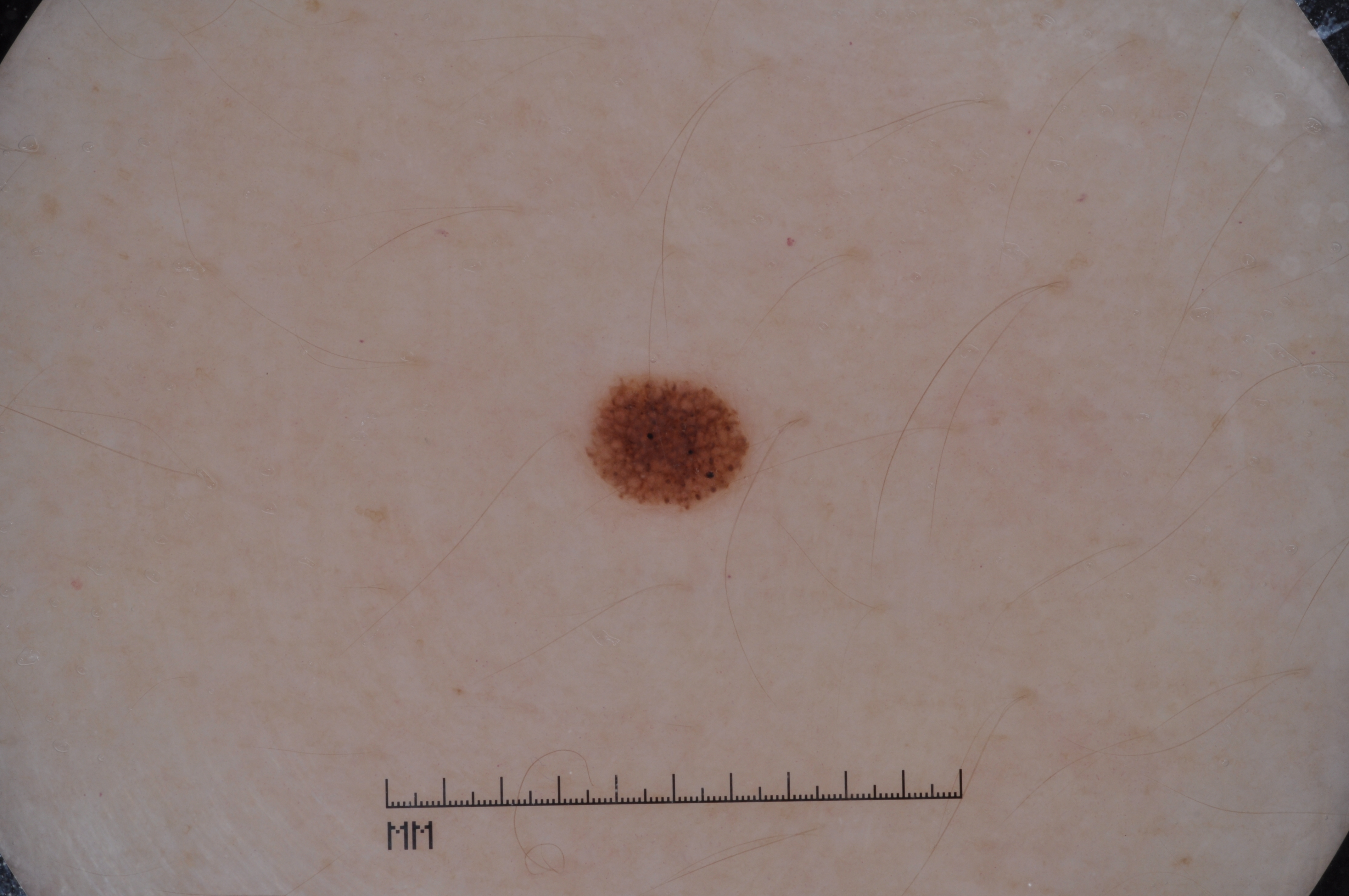Case summary:
- subject — female, aged approximately 35
- modality — dermatoscopic image of a skin lesion
- dermoscopic findings — pigment network; absent: streaks, milia-like cysts, and negative network
- size — small
- lesion bbox — bbox(590, 378, 748, 504)
- diagnosis — a melanocytic nevus, a benign skin lesion